A dermoscopic close-up of a skin lesion.
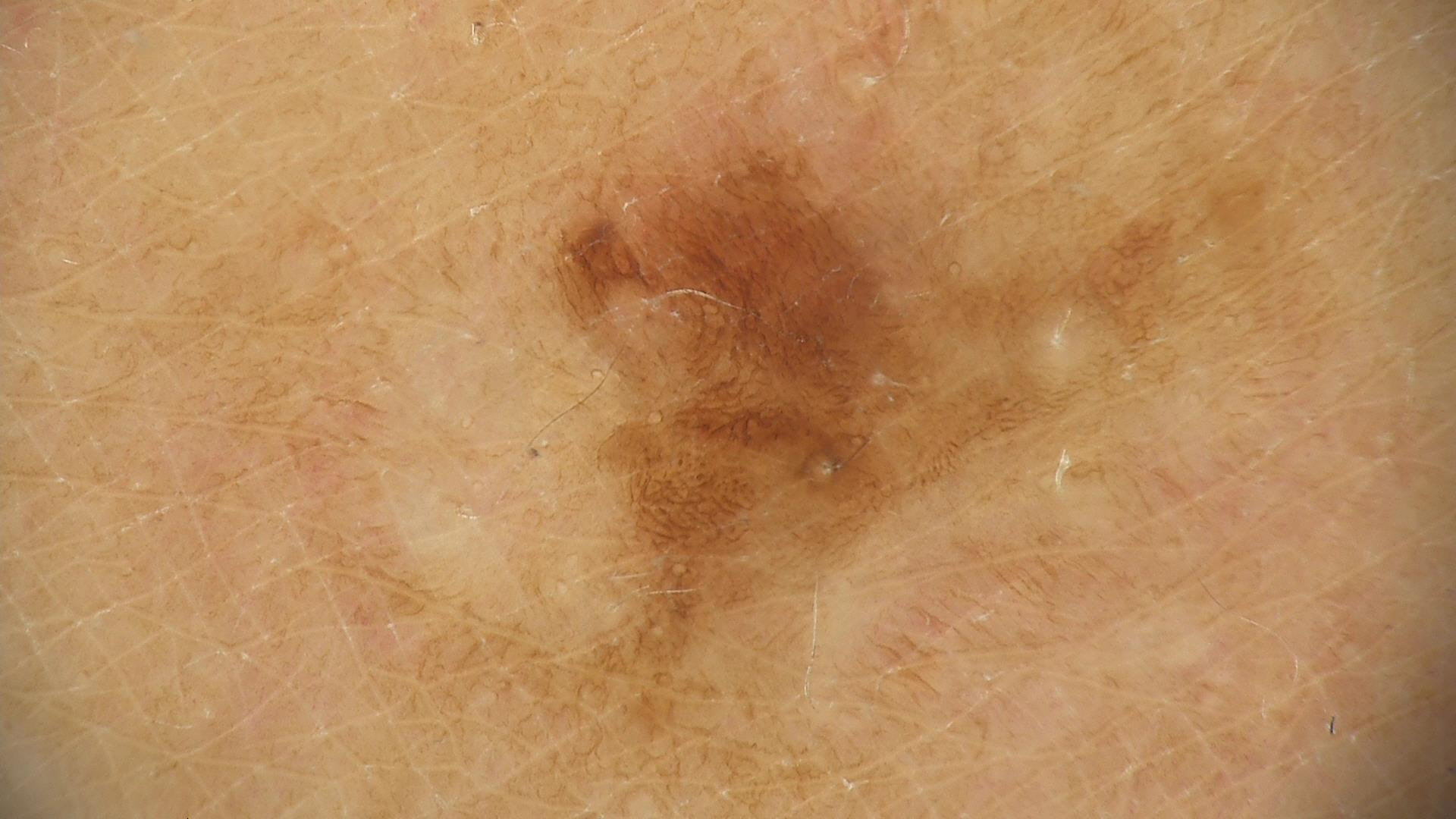Case:
• classification · dysplastic
• diagnosis · recurrent nevus (expert consensus)